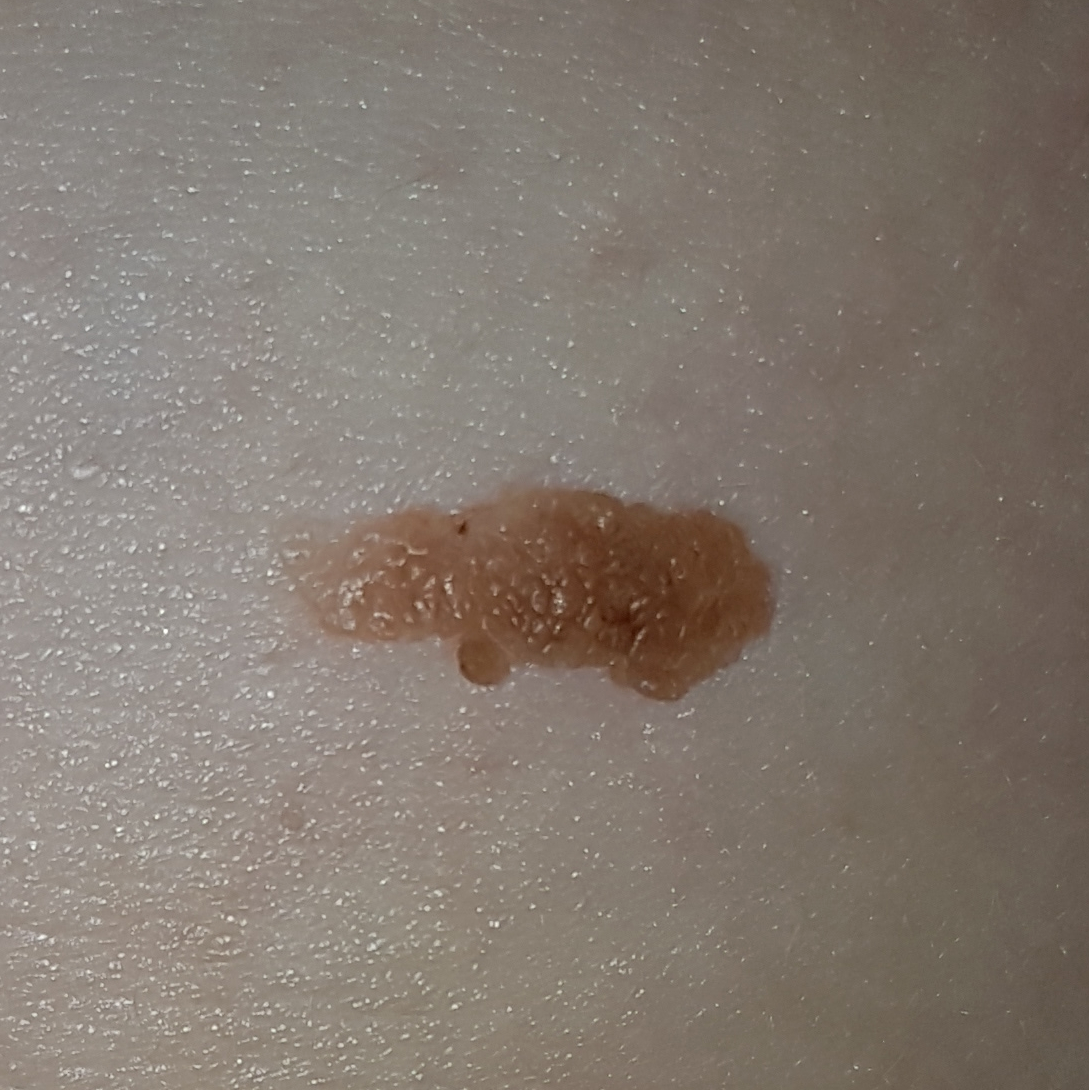{
  "diagnosis": {
    "name": "nevus",
    "code": "NEV",
    "malignancy": "benign",
    "confirmation": "clinical consensus"
  }
}